A dermoscopic image of a skin lesion.
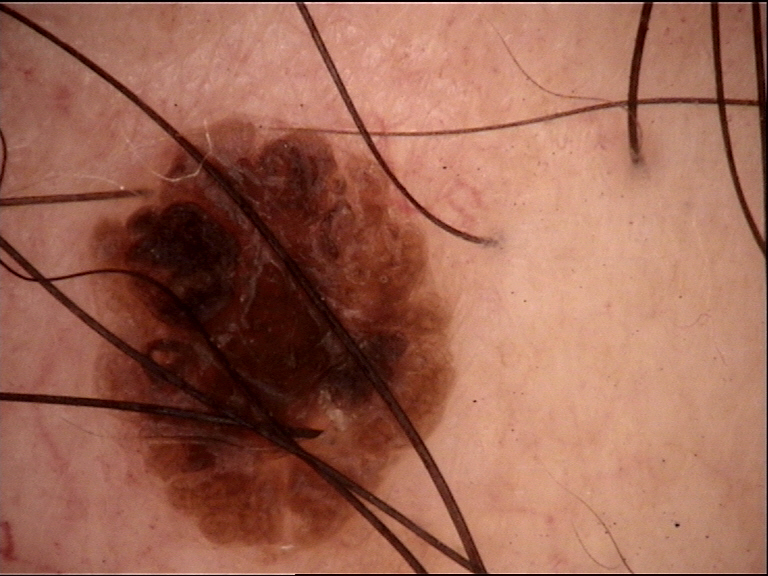Findings:
* subtype · banal
* assessment · compound nevus (expert consensus)